A dermoscopic image of a skin lesion:
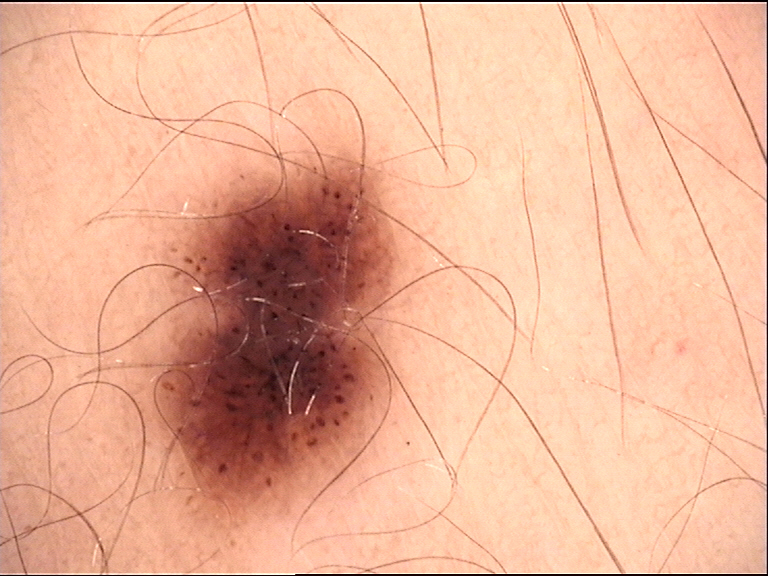Diagnosed as a dysplastic junctional nevus.